A close-up photograph.
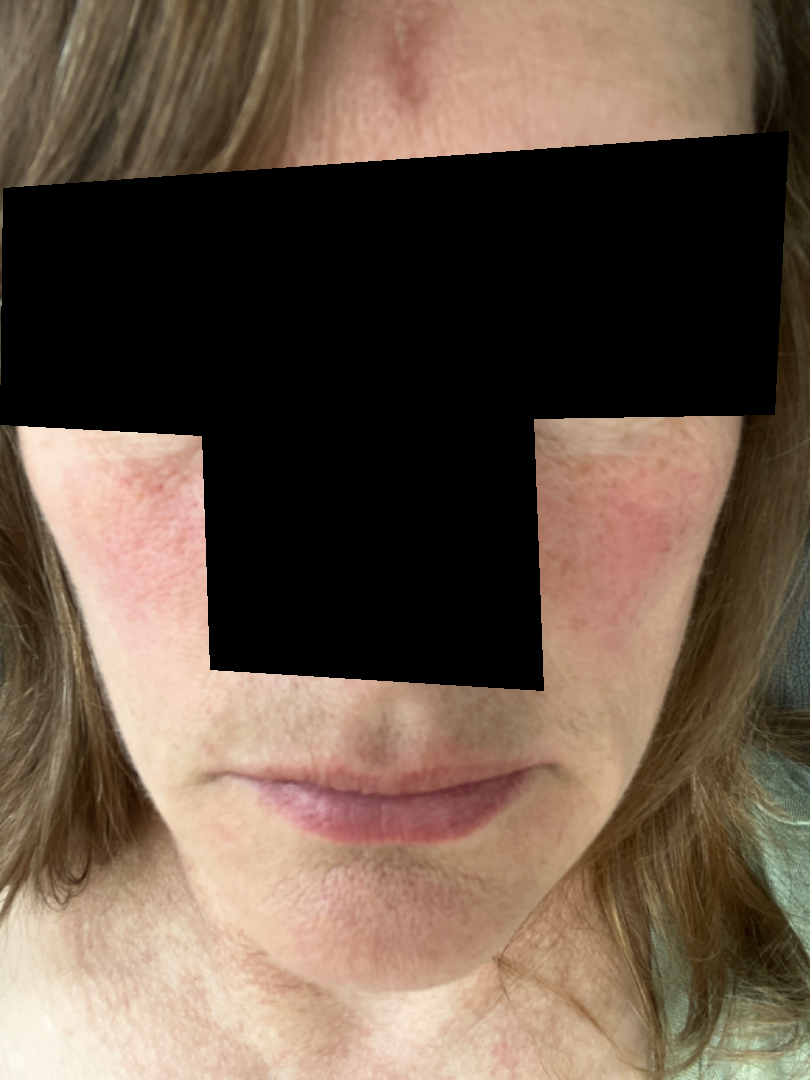Review: The skin condition could not be confidently assessed from this image.